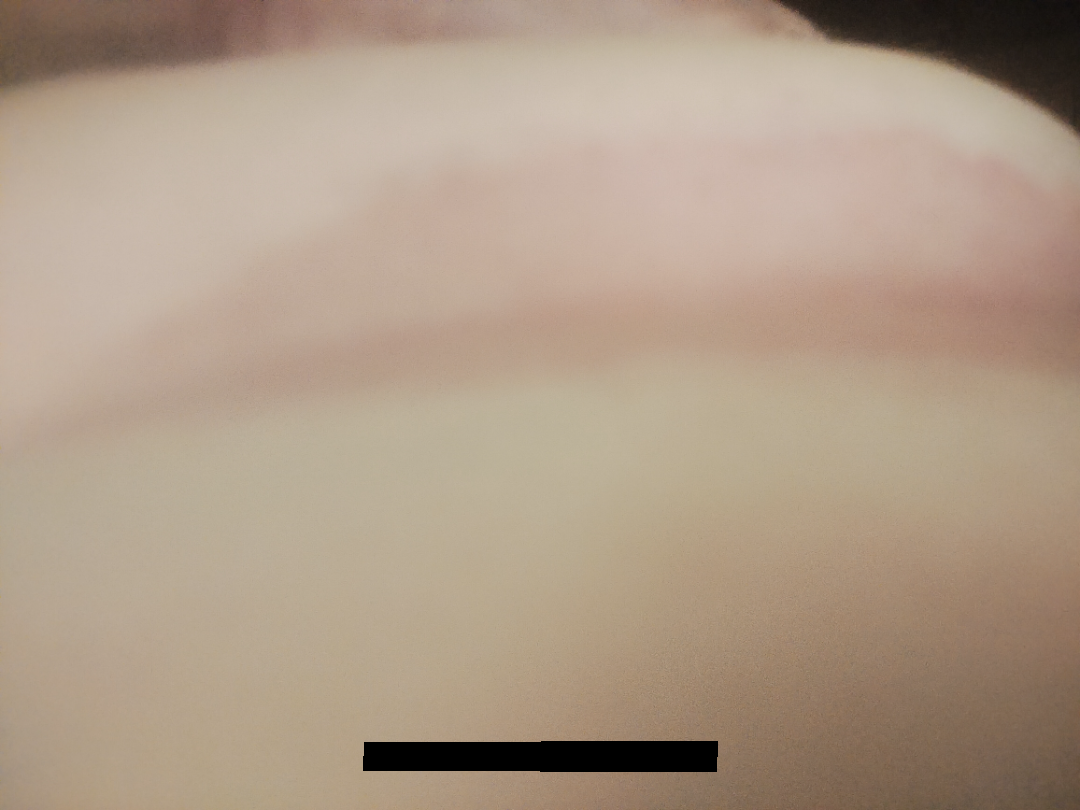The reviewing dermatologist was unable to assign a differential diagnosis from the image. The patient did not report lesion symptoms. The contributor is a female aged 60–69. The lesion is described as raised or bumpy. The photograph is a close-up of the affected area. No constitutional symptoms were reported. Present for one to four weeks.